Dermoscopy of a skin lesion.
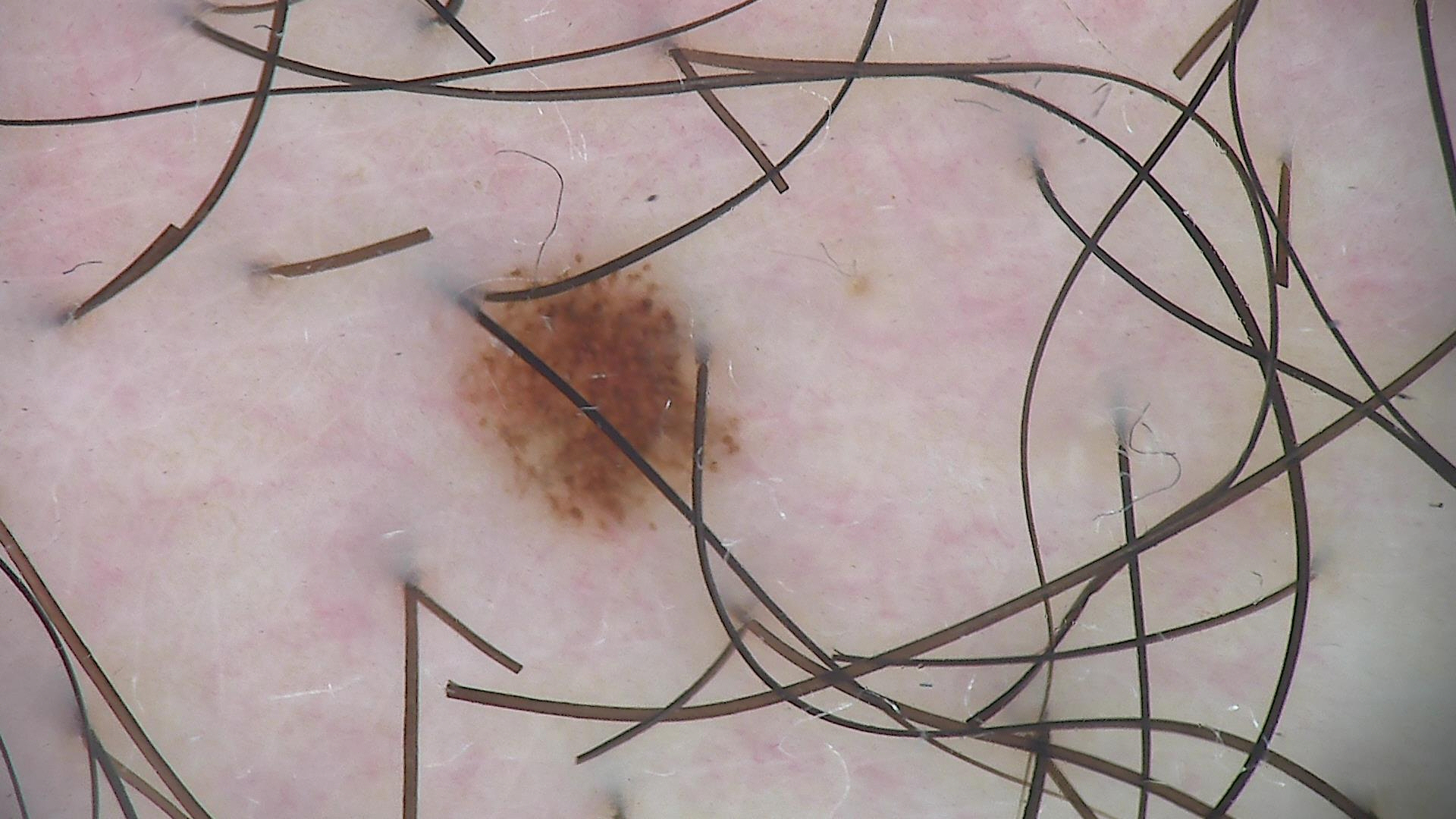Diagnosed as a benign lesion — a dysplastic junctional nevus.